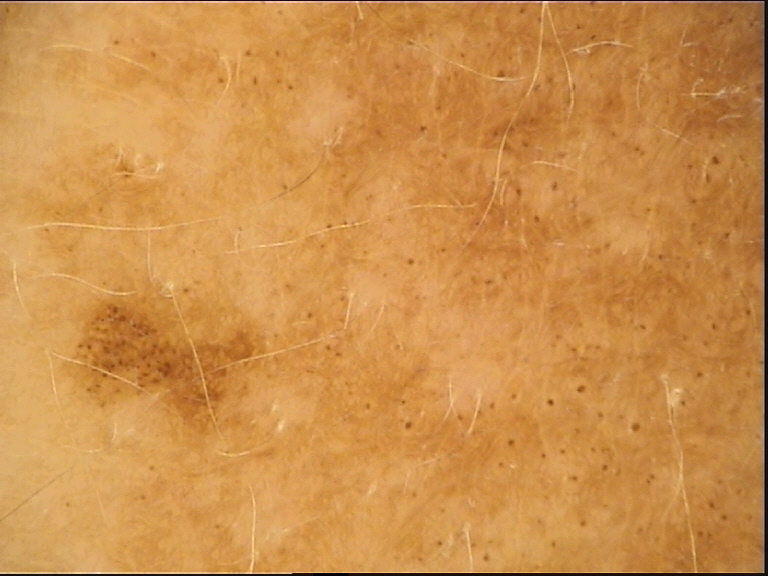imaging: dermatoscopy; lesion type: banal; assessment: congenital junctional nevus (expert consensus).